This image was taken at a distance. Female contributor, age 30–39. Located on the arm — 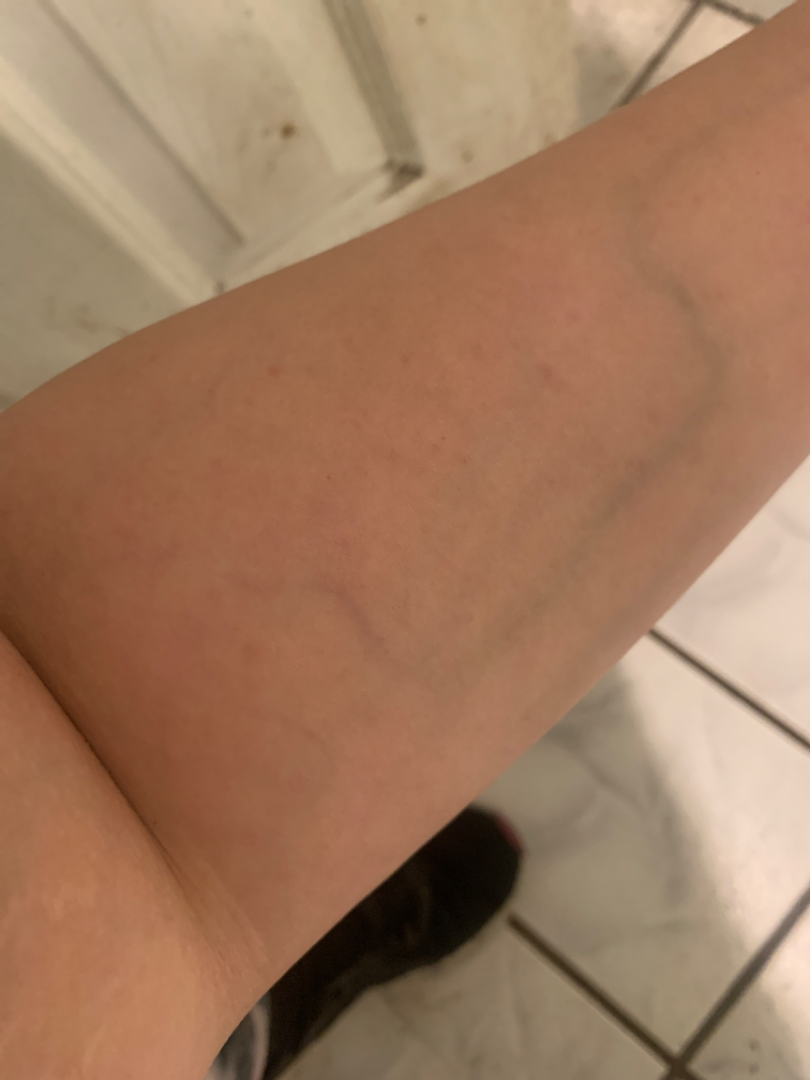Self-categorized by the patient as a rash. Symptoms reported: bothersome appearance. Fitzpatrick phototype II. The patient notes the lesion is raised or bumpy. The patient reported no systemic symptoms. The condition has been present for about one day. Three independent reviewers: most consistent with Insect Bite; also consider Eczema; with consideration of Molluscum Contagiosum.